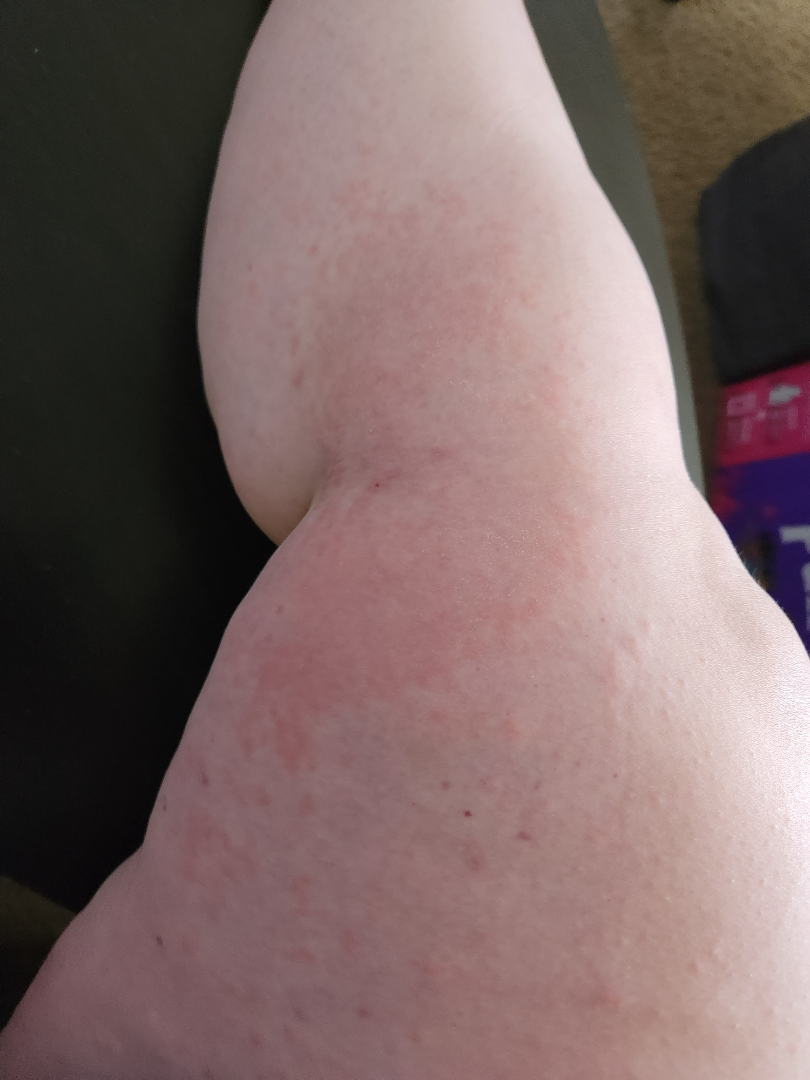On remote review of the image, the leading consideration is Eczema; less probable is Urticaria; less likely is Allergic Contact Dermatitis.